A skin lesion imaged with a dermatoscope: 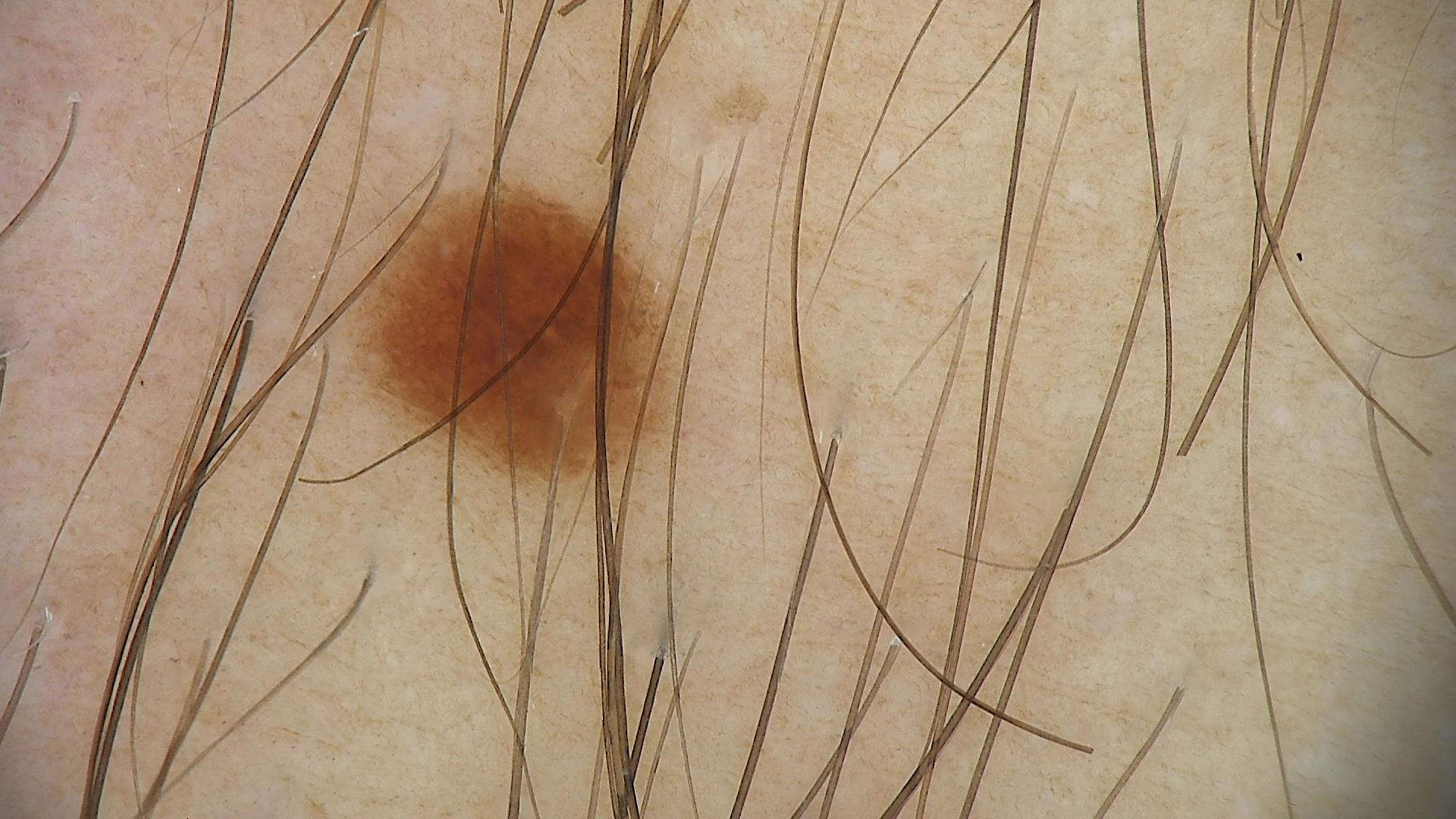| feature | finding |
|---|---|
| label | dysplastic junctional nevus (expert consensus) |